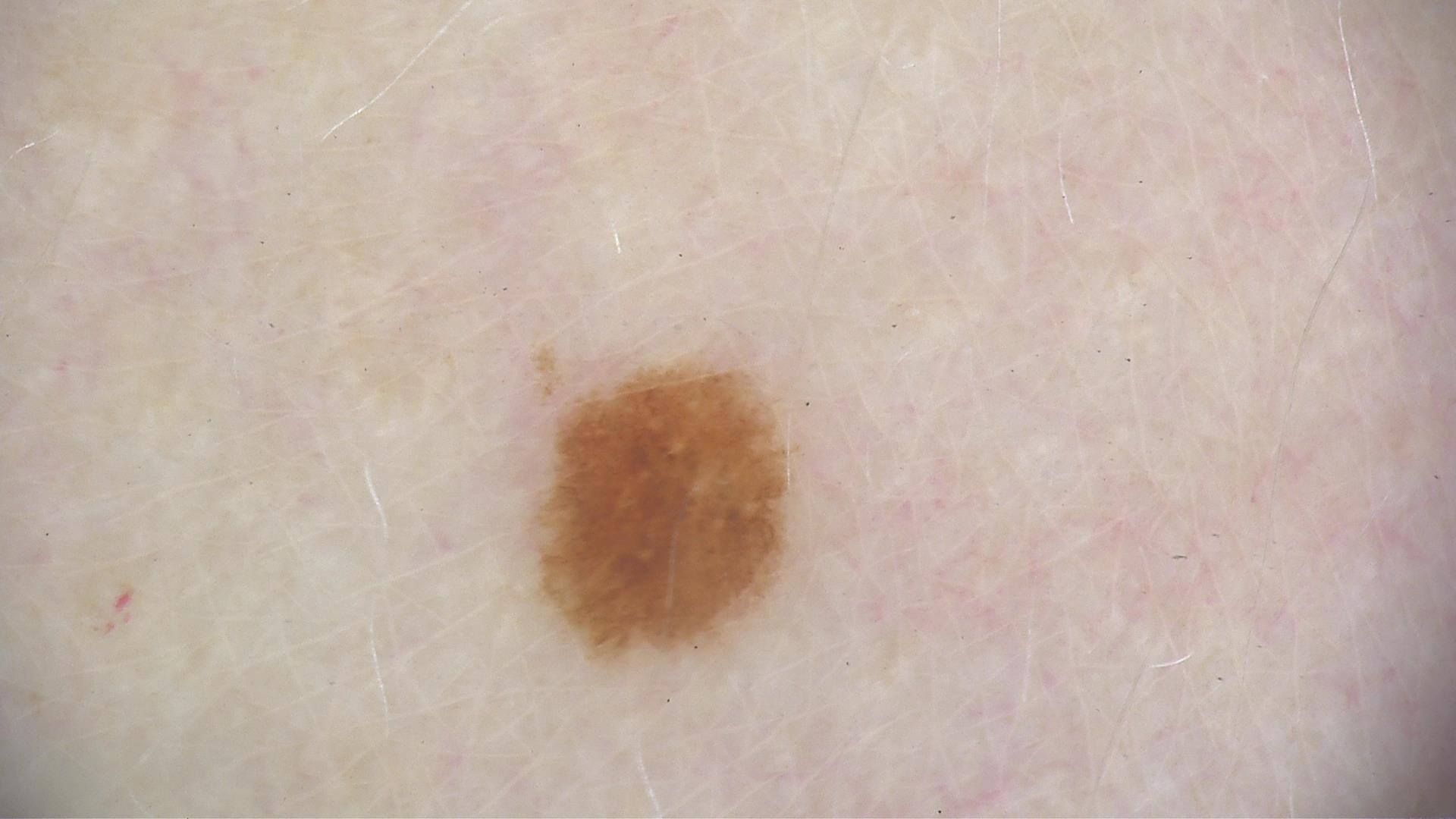Impression: The diagnosis was a dysplastic junctional nevus.